The lesion involves the front of the torso, leg and head or neck · the contributor reports the lesion is raised or bumpy · FST III · close-up view:
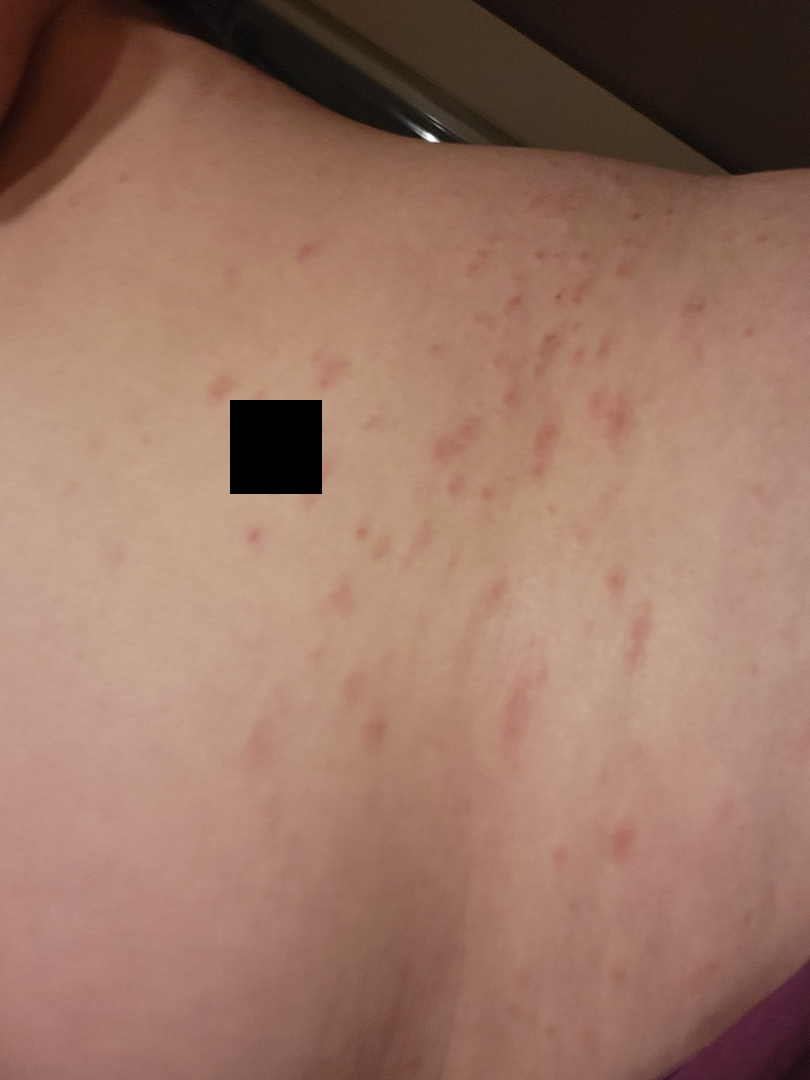The skin findings could not be characterized from the image.